The lesion is described as raised or bumpy; close-up view; present for about one day; the affected area is the front of the torso: 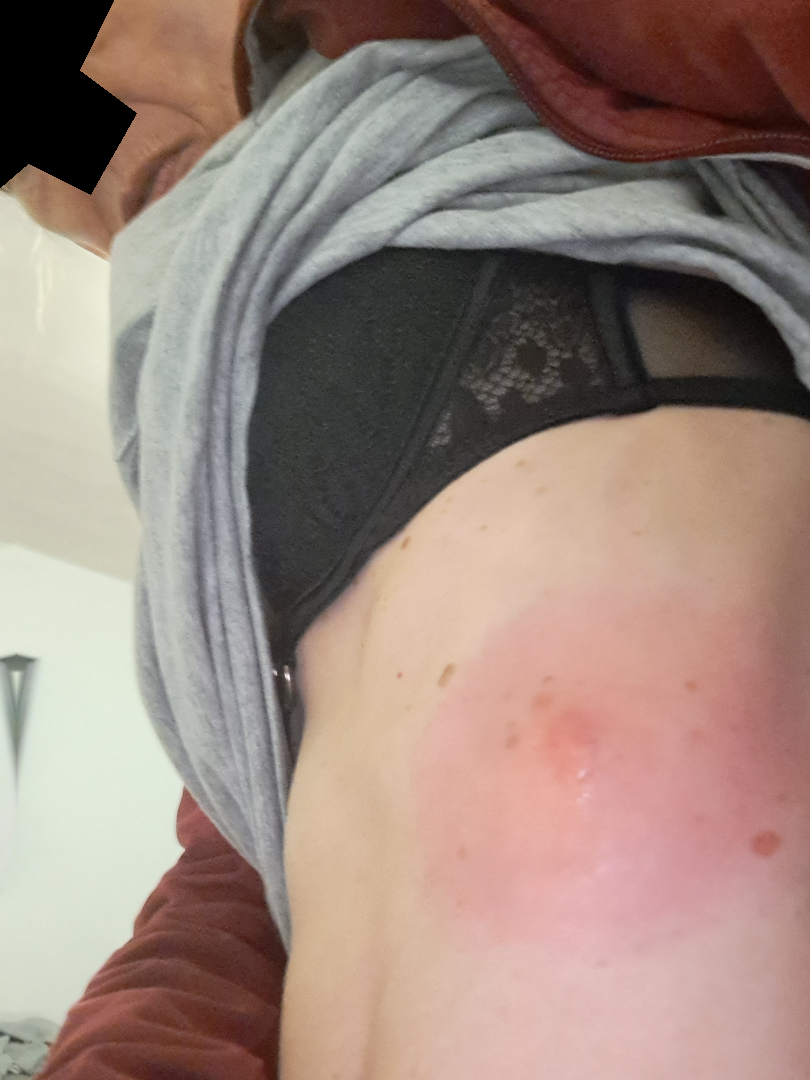Q: Could the case be diagnosed?
A: indeterminate from the photograph